The condition has been present for one to four weeks; close-up view; the patient reports the lesion is raised or bumpy and rough or flaky; the contributor is 30–39, female; symptoms reported: itching and bothersome appearance; the lesion involves the arm:
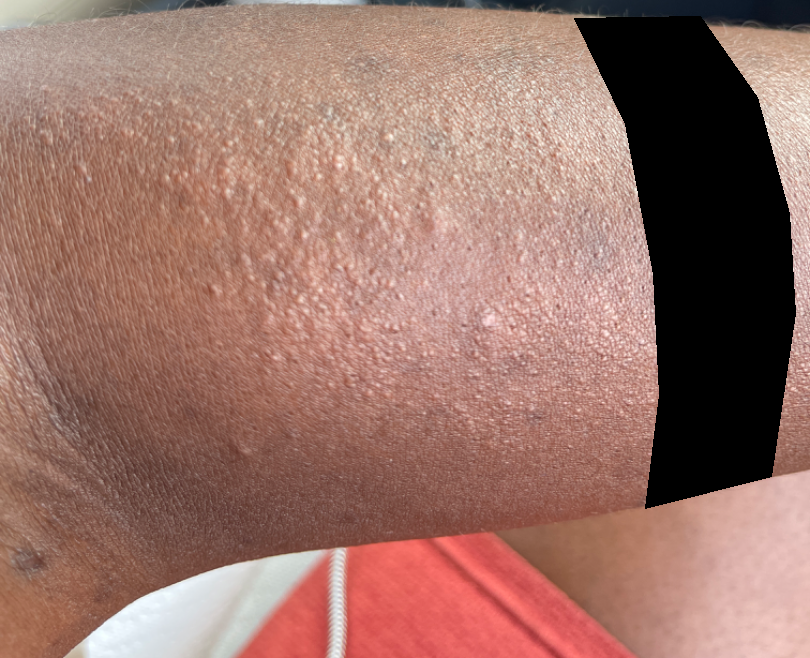Case summary:
- dermatologist impression · three dermatologists each reviewed the case: Eczema and Allergic Contact Dermatitis were each considered, in no particular order; a more distant consideration is Photodermatitis